A close-up photograph. Located on the leg:
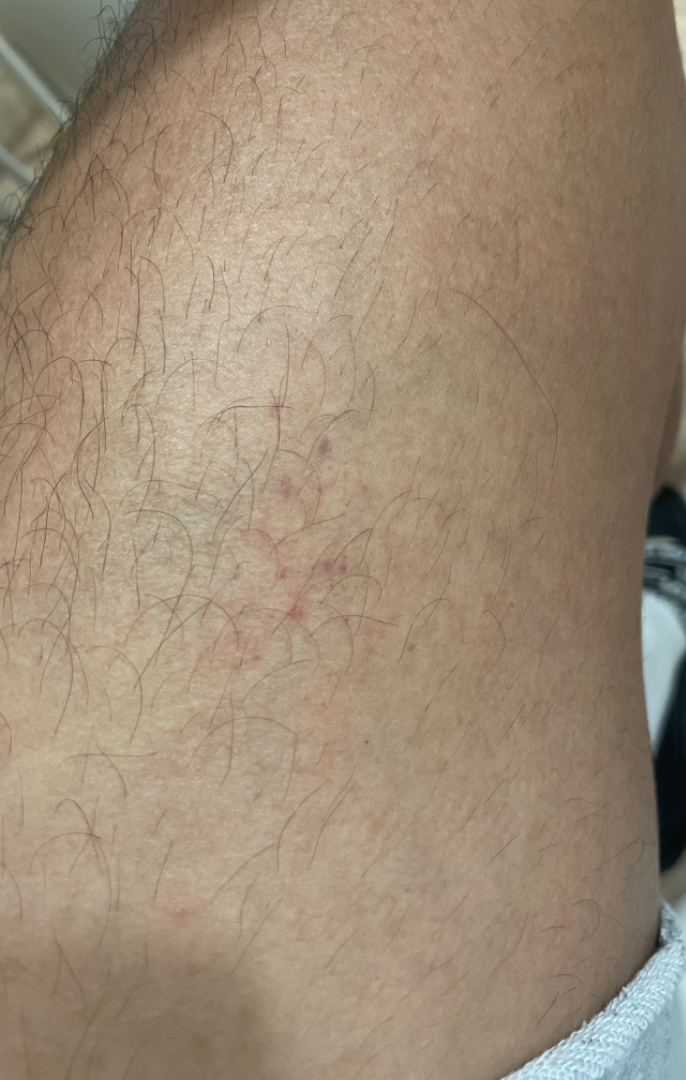Assessment:
The image was not sufficient for the reviewer to characterize the skin condition.
Clinical context:
Reported duration is about one day. The lesion is described as flat. Skin tone: Fitzpatrick skin type IV. Self-categorized by the patient as a rash. No relevant systemic symptoms.